Close-up view, reported lesion symptoms include itching, skin tone: Fitzpatrick skin type II; non-clinician graders estimated a MST of 2, no constitutional symptoms were reported: 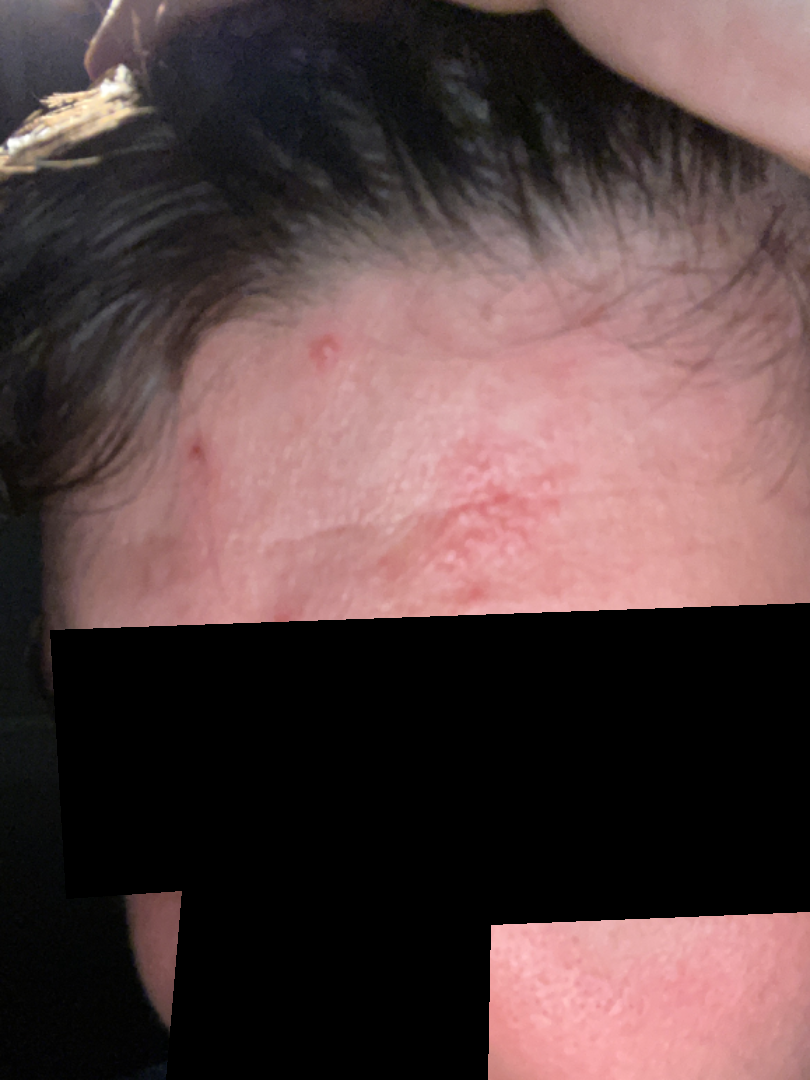Q: What was the assessment?
A: not assessable